Associated systemic symptoms include shortness of breath · the photo was captured at an angle · male patient, age 60–69: 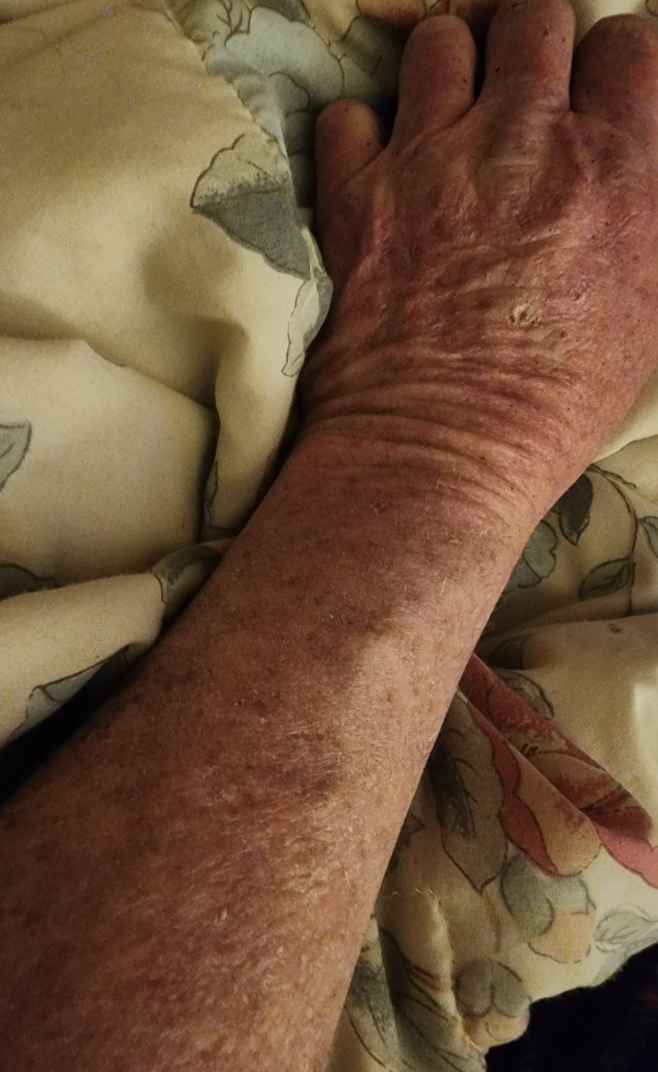Assessment: The image was not sufficient for the reviewer to characterize the skin condition.